A dermoscopic image of a skin lesion: 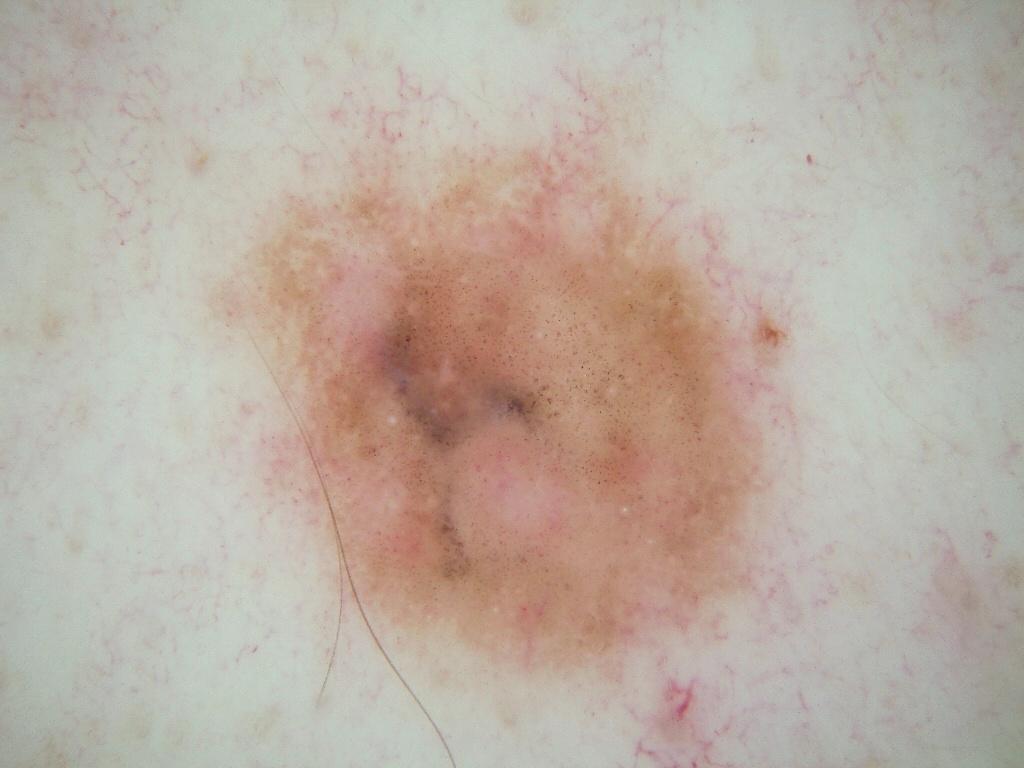With coordinates (x1, y1, x2, y2), the lesion occupies the region 195 104 802 721.
Dermoscopic review identifies milia-like cysts, negative network, and globules.
Expert review diagnosed this as a melanocytic nevus.